Dermoscopy of a skin lesion, the patient is male: 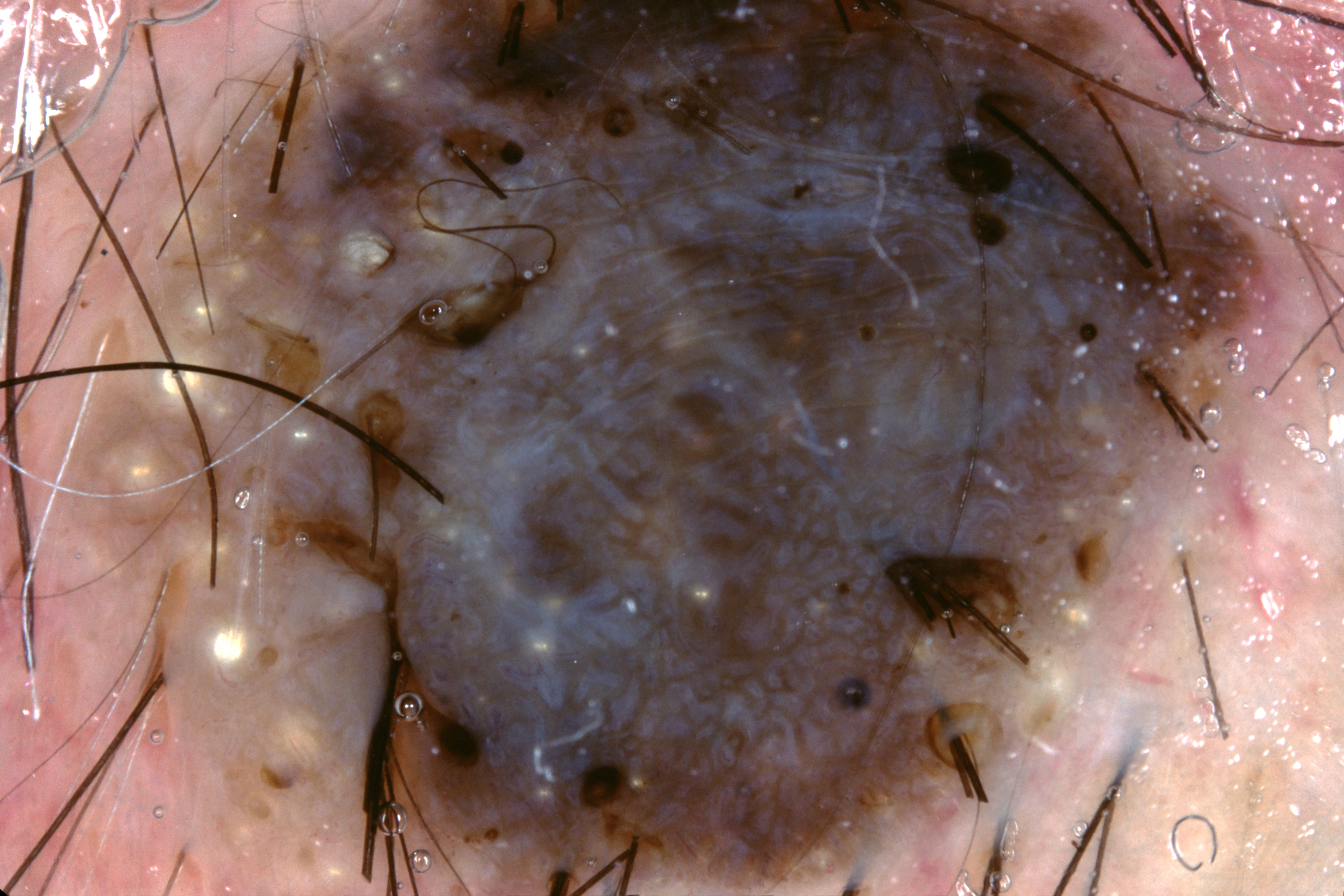The lesion takes up about 71% of the image.
Dermoscopic assessment notes milia-like cysts, with no negative network, pigment network, or streaks.
In (x1, y1, x2, y2) order, the lesion occupies the region (73, 10, 1274, 889).
The clinical diagnosis was a seborrheic keratosis, a lesion of keratinocytic origin.